A female patient 44 years of age · a clinical photograph of a skin lesion — 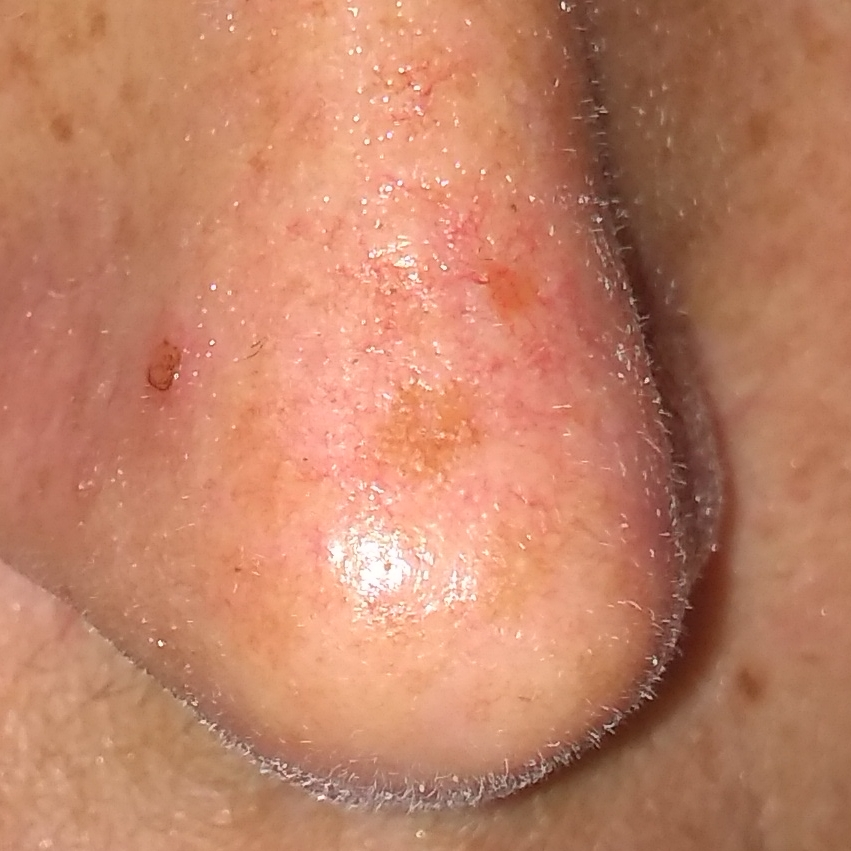location=the nose | symptoms=itching | diagnosis=basal cell carcinoma (biopsy-proven).